This image was taken at an angle · the lesion involves the top or side of the foot · the subject is a female aged 18–29: 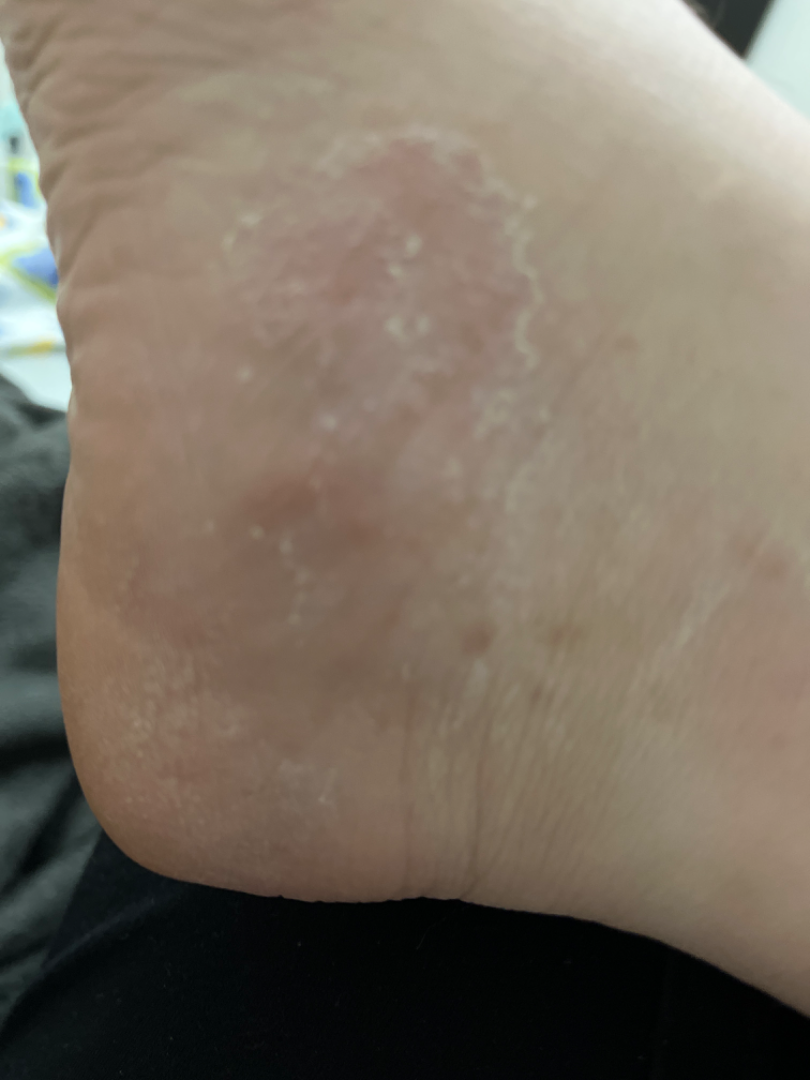{
  "assessment": "ungradable on photographic review",
  "symptoms": [
    "bothersome appearance",
    "itching",
    "burning"
  ]
}